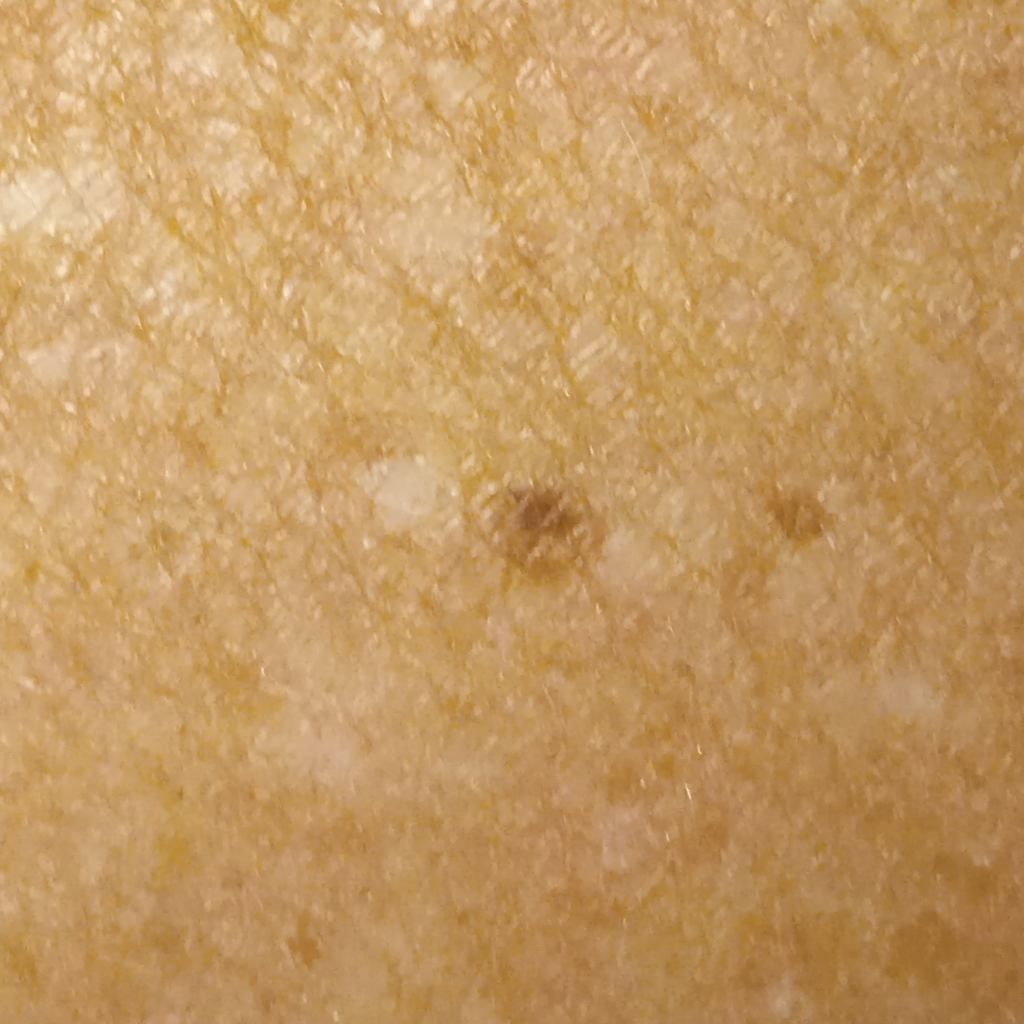| feature | finding |
|---|---|
| diagnostic label | melanocytic nevus (dermatologist consensus) |